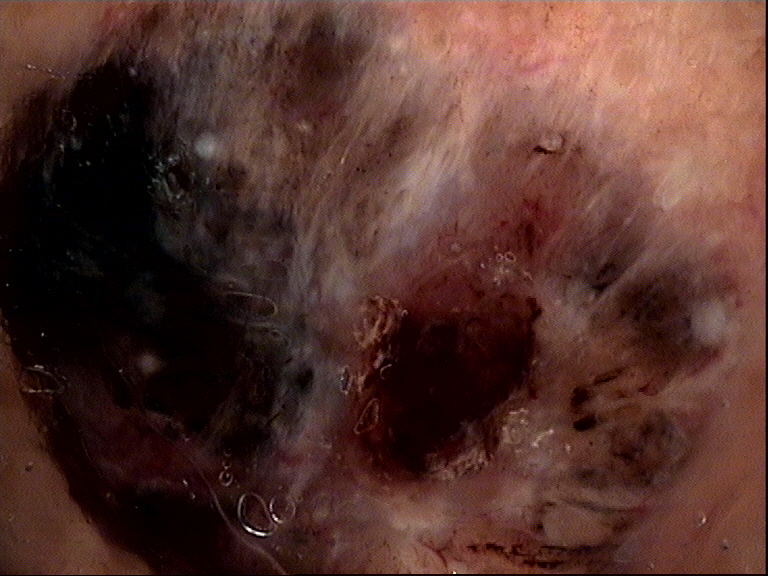Findings:
A dermoscopy image of a single skin lesion.
Pathology:
Biopsy-confirmed as a malignant lesion — a basal cell carcinoma.